This is a close-up image.
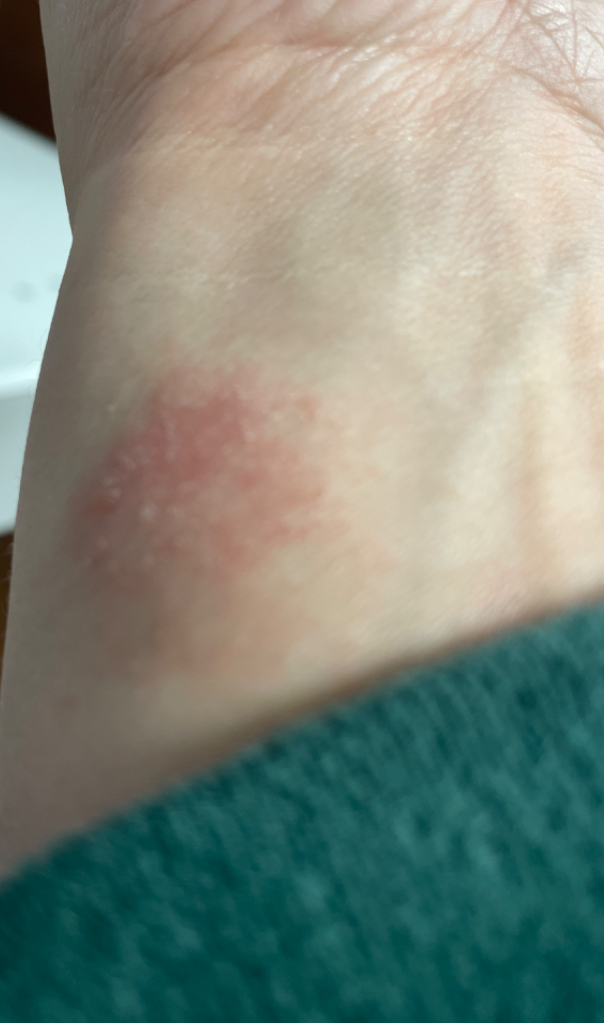  assessment: indeterminate from the photograph